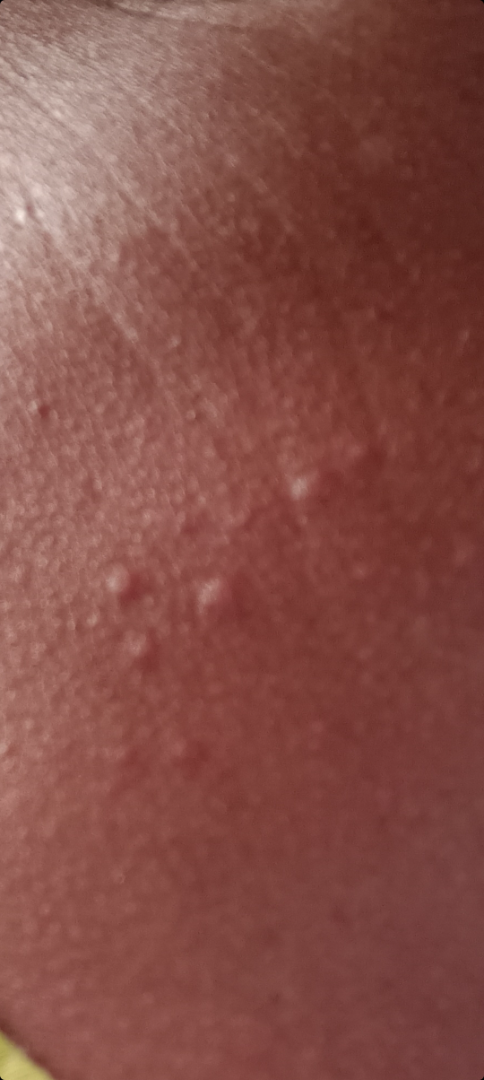The dermatologist could not determine a likely condition from the photograph alone. Fitzpatrick phototype IV; non-clinician graders estimated Monk Skin Tone 2 or 5. The subject is a female aged 50–59. Present for about one day. The patient considered this skin that appeared healthy to them. Texture is reported as fluid-filled and raised or bumpy. The lesion is associated with pain and burning. The photograph is a close-up of the affected area.